A dermatoscopic image of a skin lesion.
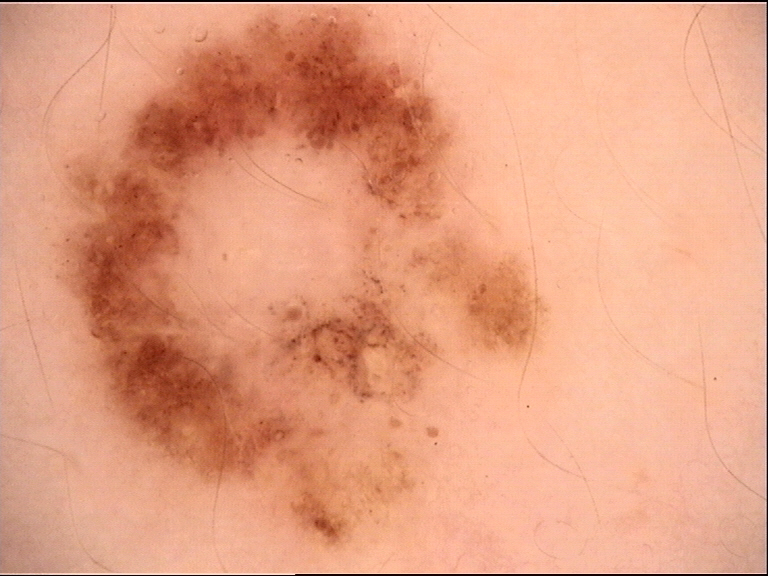The diagnosis was a dysplastic junctional nevus.